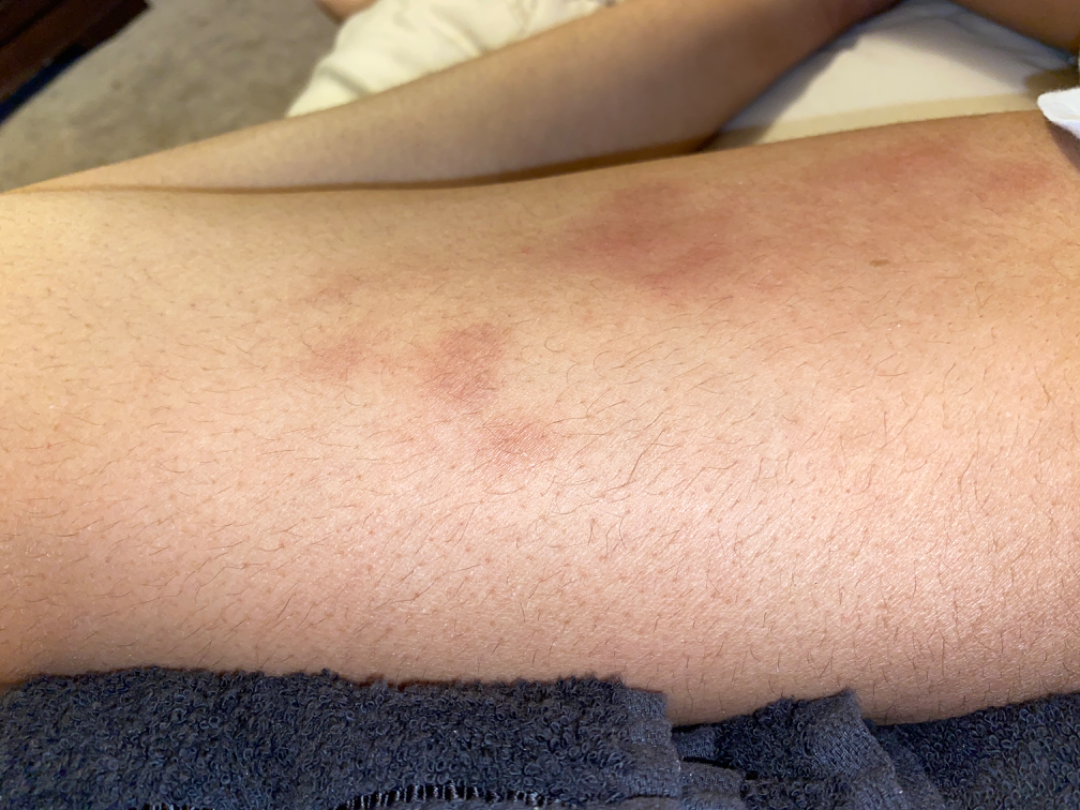The patient indicates darkening and bothersome appearance.
This image was taken at an angle.
The lesion involves the leg.
The lesion is described as rough or flaky.
The patient indicates associated chills, fever and joint pain.
The patient considered this a rash.
Skin tone: Fitzpatrick phototype III.
Reported duration is one to four weeks.
Kaposi's sarcoma of skin and ecchymoses were considered with similar weight; a more distant consideration is resolving dermatitis.